The photo was captured at an angle · the lesion is described as raised or bumpy · Fitzpatrick III · the patient reports the condition has been present for less than one week · the lesion involves the leg:
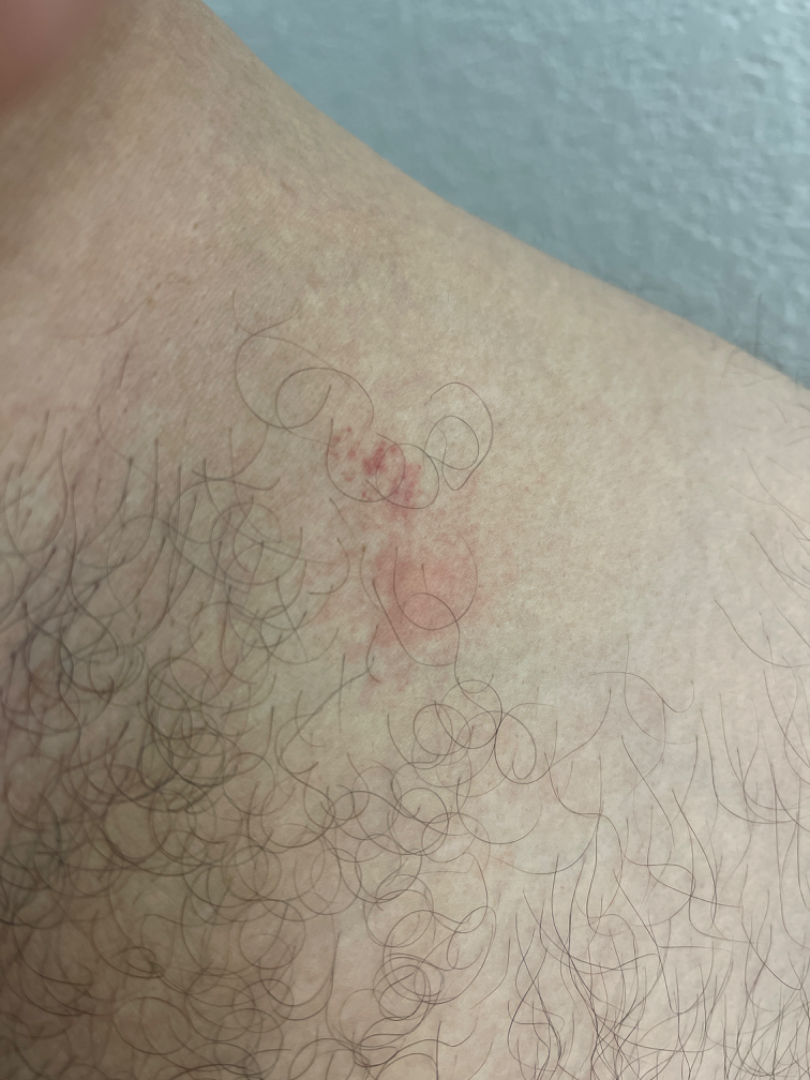| key | value |
|---|---|
| assessment | consistent with Eczema |